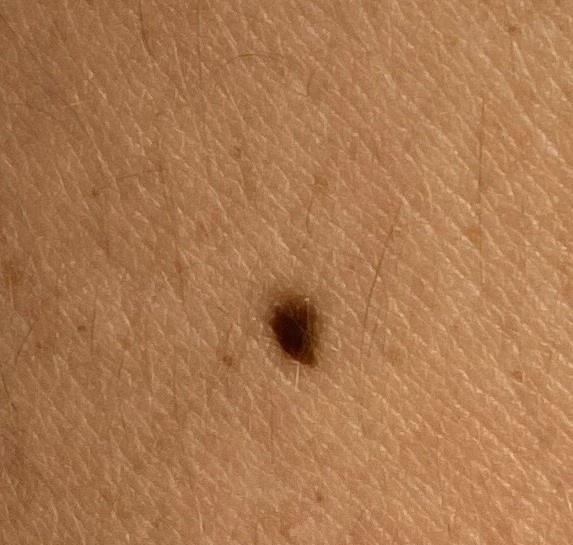{
  "patient": {
    "age_approx": 30,
    "sex": "male"
  },
  "image": "clinical overview photograph",
  "skin_type": "II",
  "lesion_location": {
    "region": "the trunk",
    "detail": "the posterior trunk"
  },
  "diagnosis": {
    "name": "Nevus",
    "malignancy": "benign",
    "confirmation": "histopathology",
    "lineage": "melanocytic"
  }
}